The condition has been present for less than one week; female subject, age 18–29; no associated systemic symptoms reported; the lesion is described as raised or bumpy; located on the front of the torso; the patient reports pain, itching and enlargement; a close-up photograph:
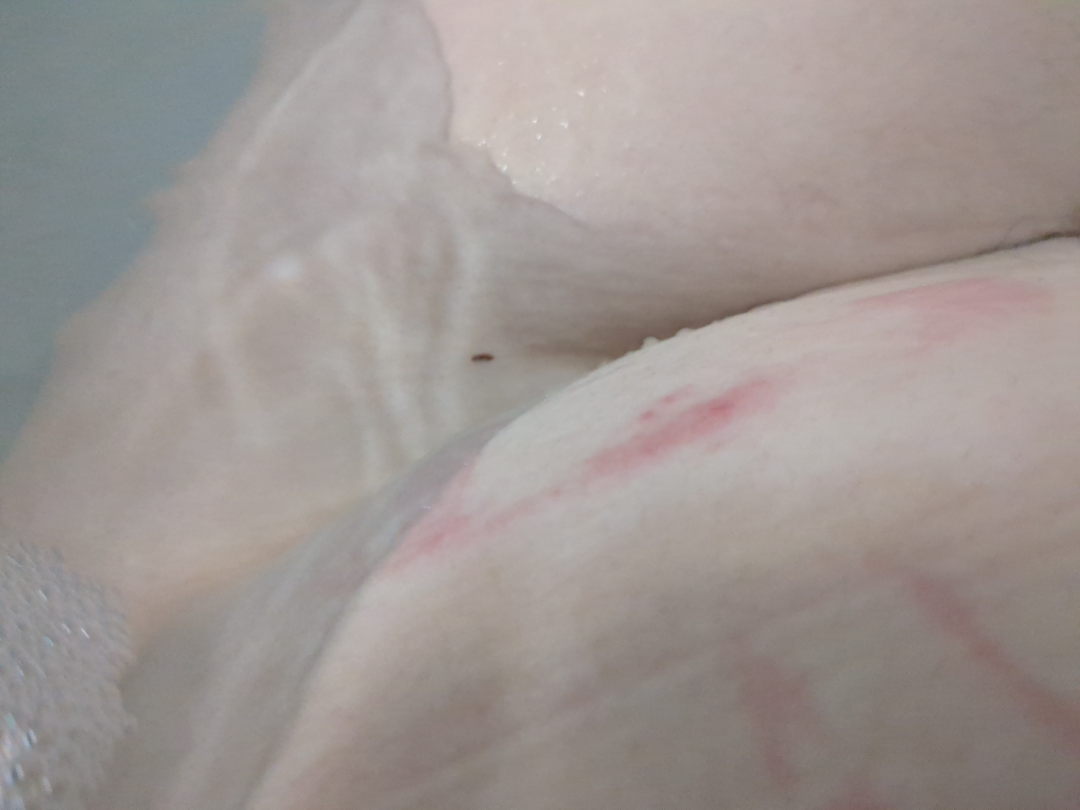dermatologist impression = three independent reviewers: most consistent with Allergic Contact Dermatitis.